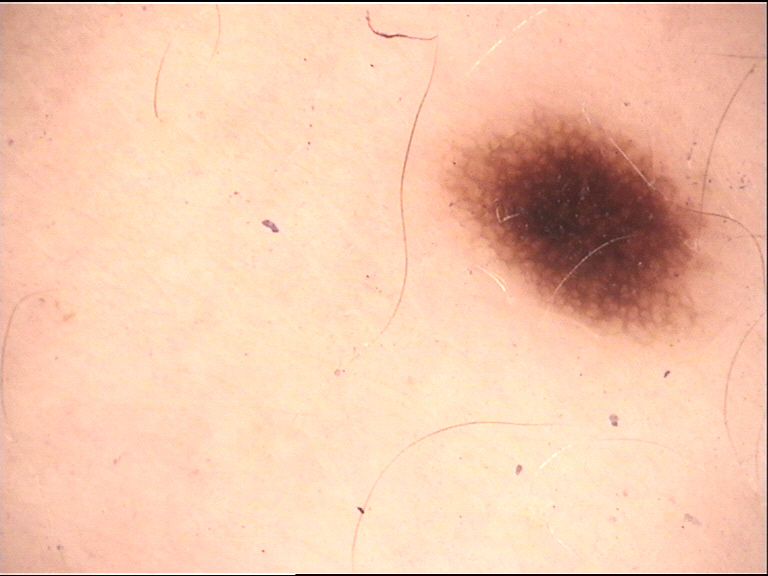A dermoscopic photograph of a skin lesion. Diagnosed as a benign lesion — a dysplastic junctional nevus.